Symptoms reported: bothersome appearance, texture is reported as rough or flaky, located on the arm, the patient is a female aged 30–39, no associated systemic symptoms reported, the patient considered this skin that appeared healthy to them, the photograph was taken at a distance: 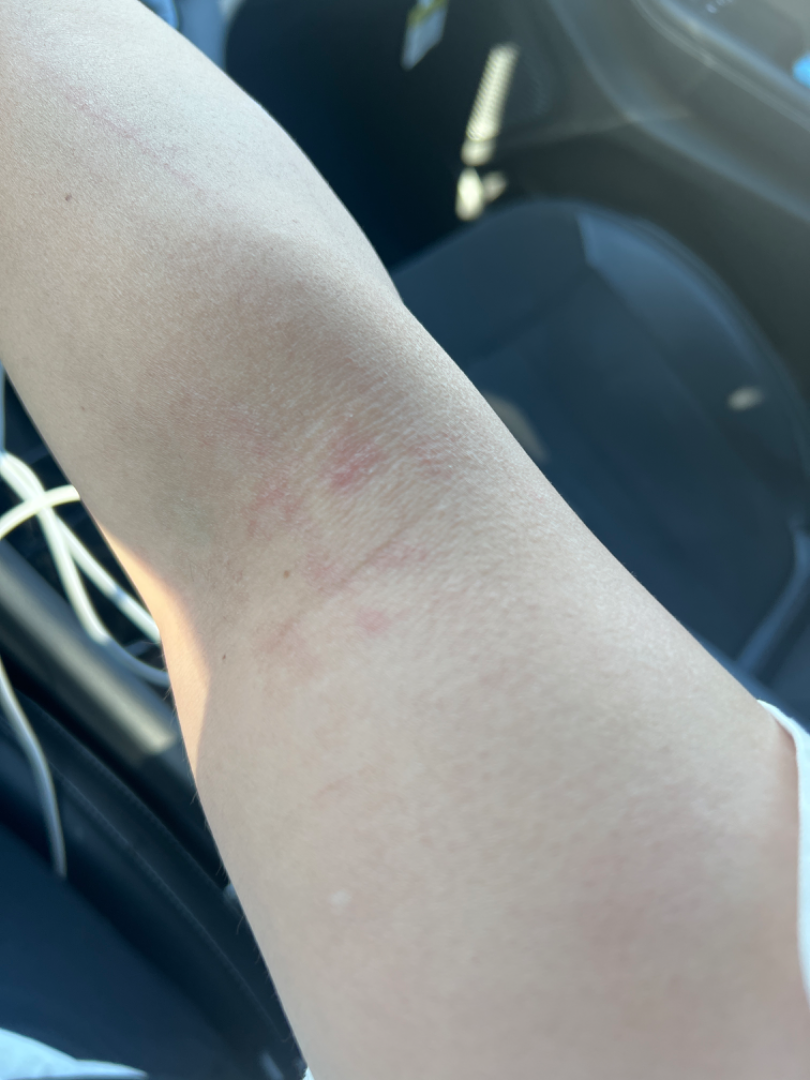Impression:
The reviewing panel's impression was: Eczema (favored).